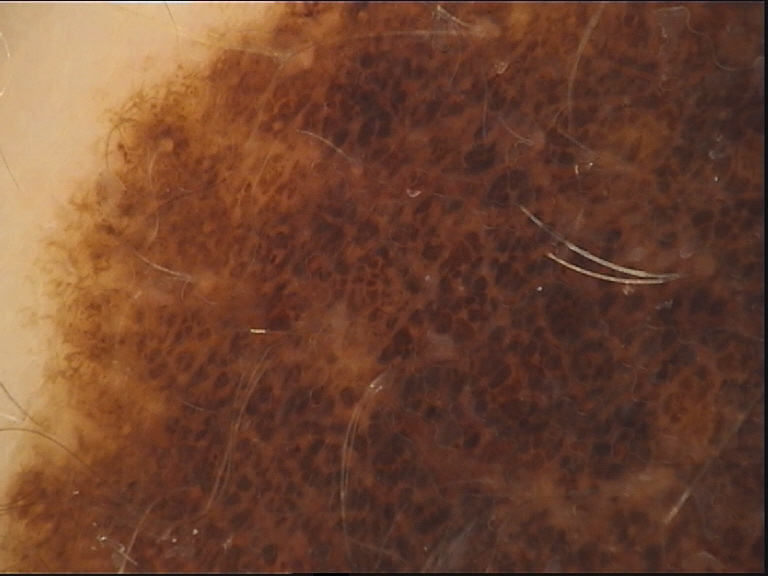A dermatoscopic image of a skin lesion.
The architecture is that of a banal lesion.
Labeled as a congenital compound nevus.